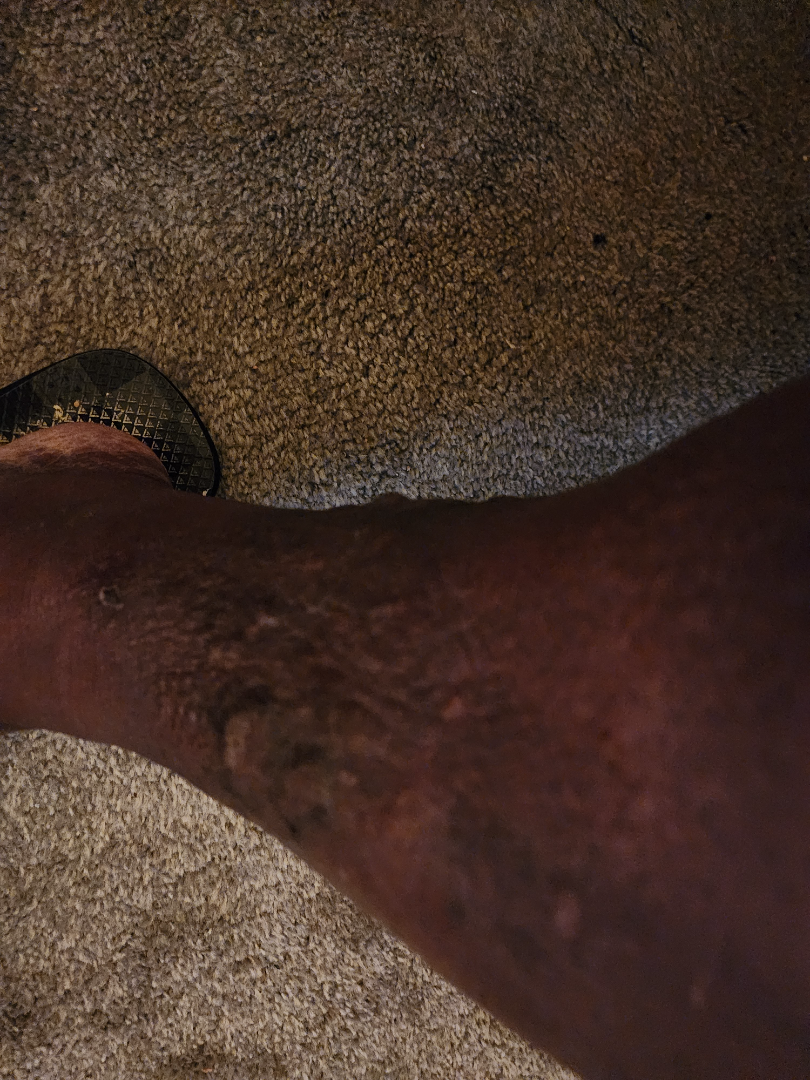Findings: The dermatologist could not determine a likely condition from the photograph alone. Background: A close-up photograph.